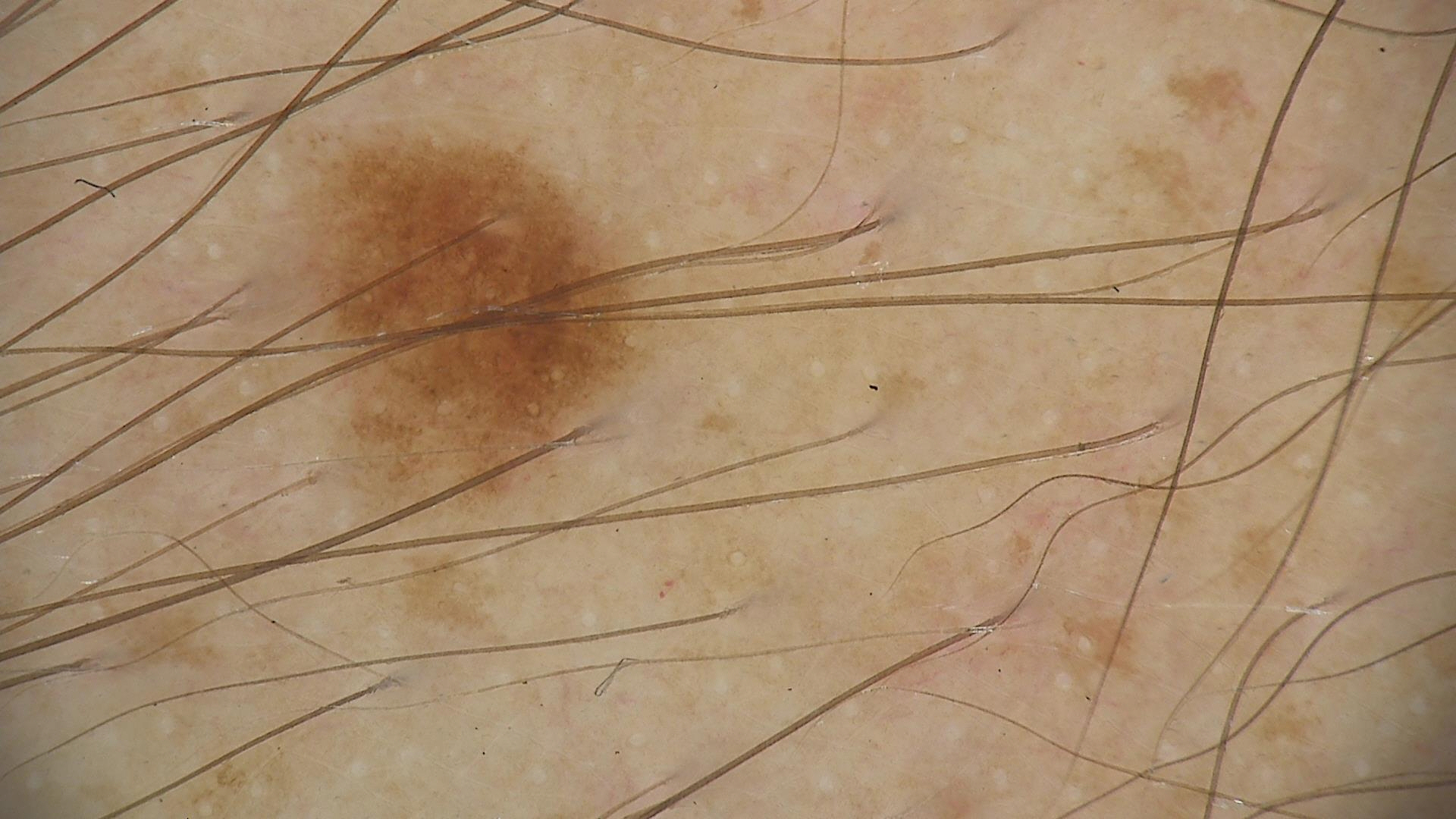A dermoscopic image of a skin lesion.
Classified as a dysplastic junctional nevus.